A dermoscopy image of a single skin lesion.
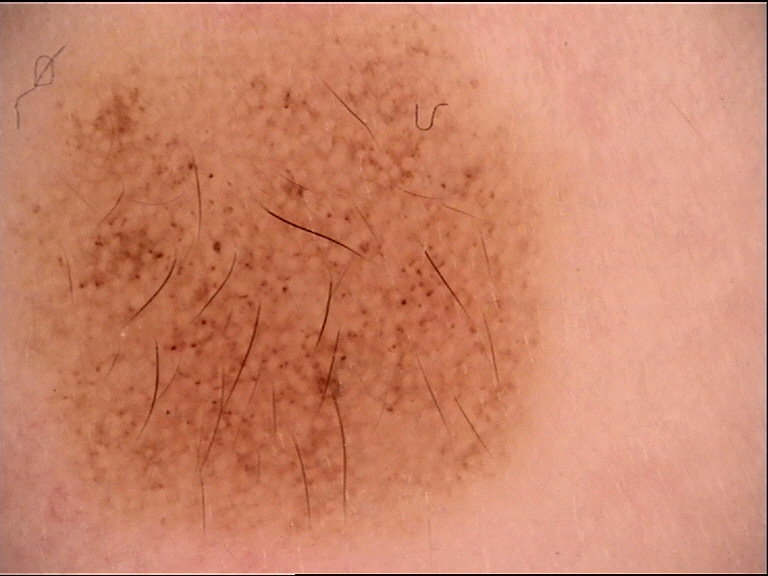subtype: banal, class: congenital junctional nevus (expert consensus).